Imaged for a research study, with no referral diagnosis recorded; a dermatoscopic image of a skin lesion — 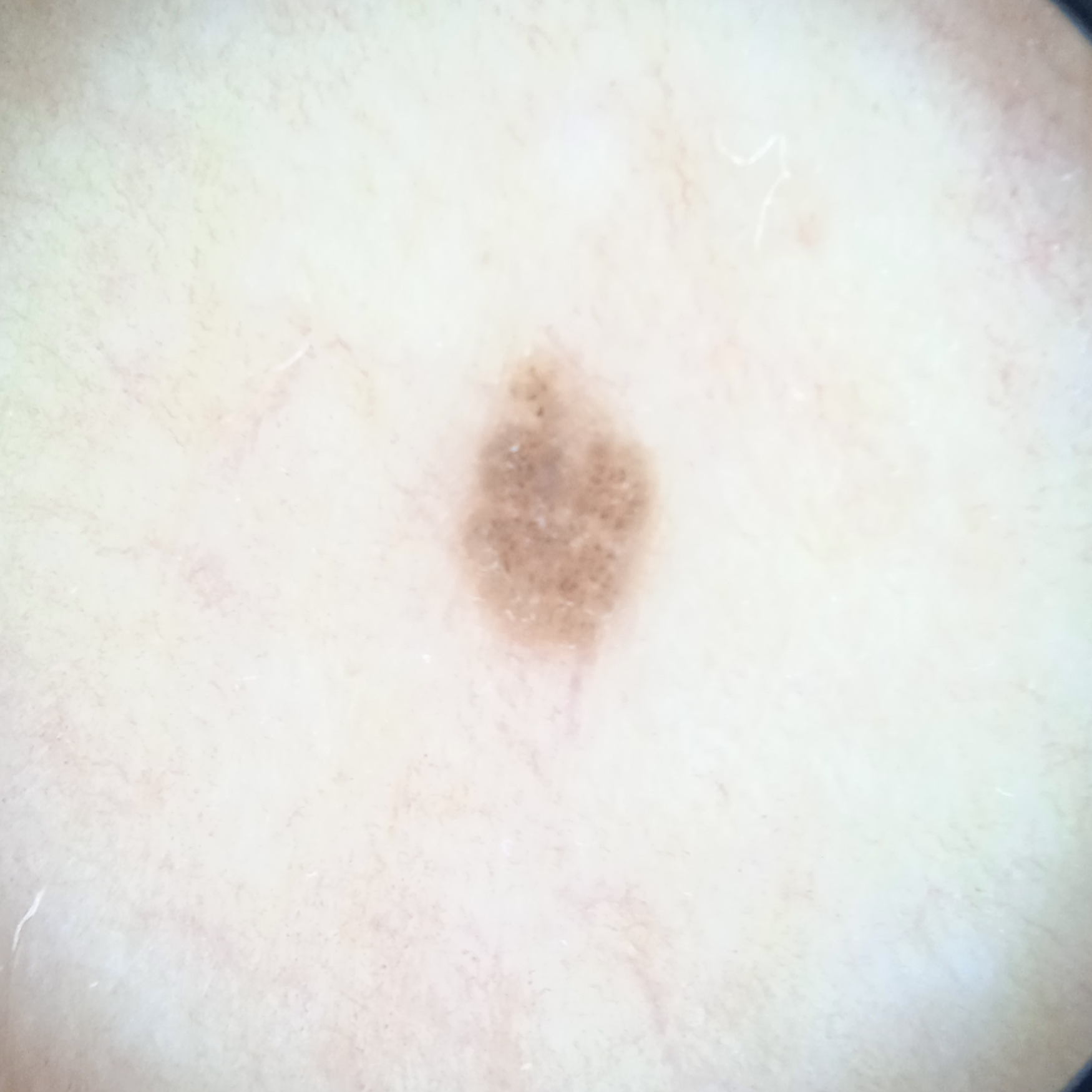Case:
- anatomic site · the torso
- diameter · 3.4 mm
- assessment · melanocytic nevus (dermatologist consensus)